By self-report, a personal history of skin cancer and a personal history of cancer · the patient says their skin tans without first burning · a female subject 60 years old · collected as part of a research study, without a referral diagnosis · the patient describes having few moles overall:
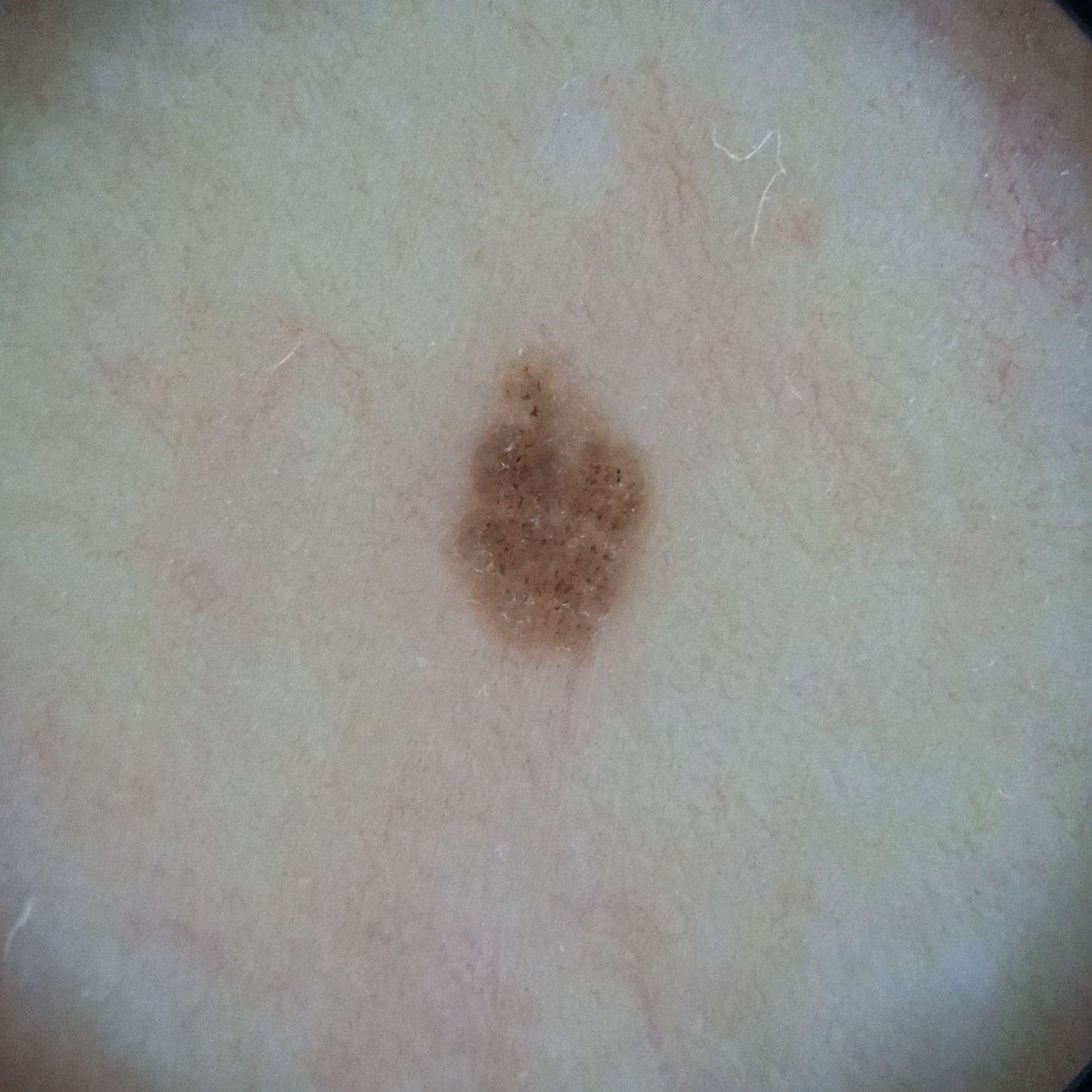Located on the torso. Measuring roughly 3.4 mm. The dermatologists' assessment was a melanocytic nevus.